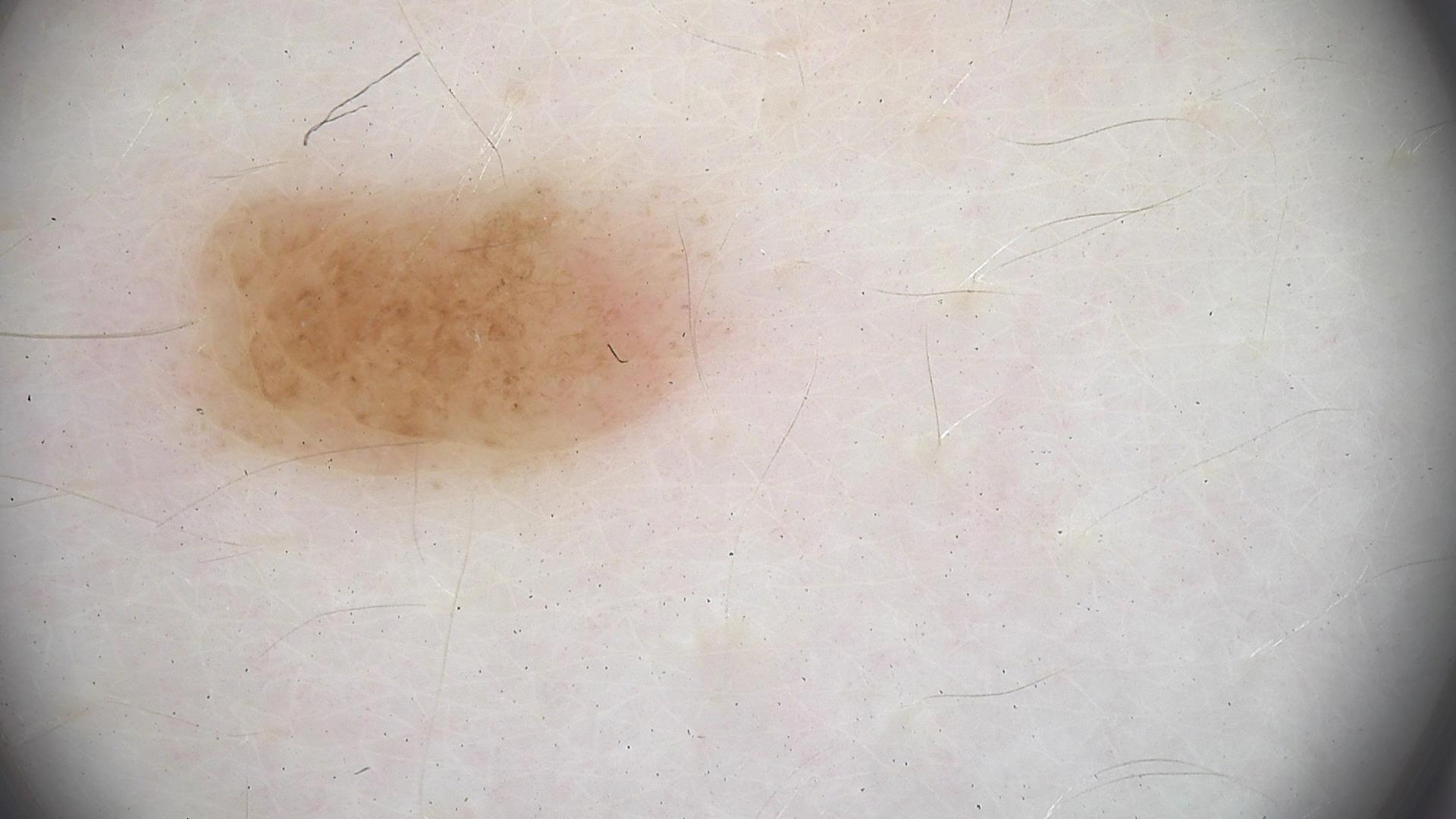classification=banal
diagnostic label=compound nevus (expert consensus)